A dermatoscopic image of a skin lesion.
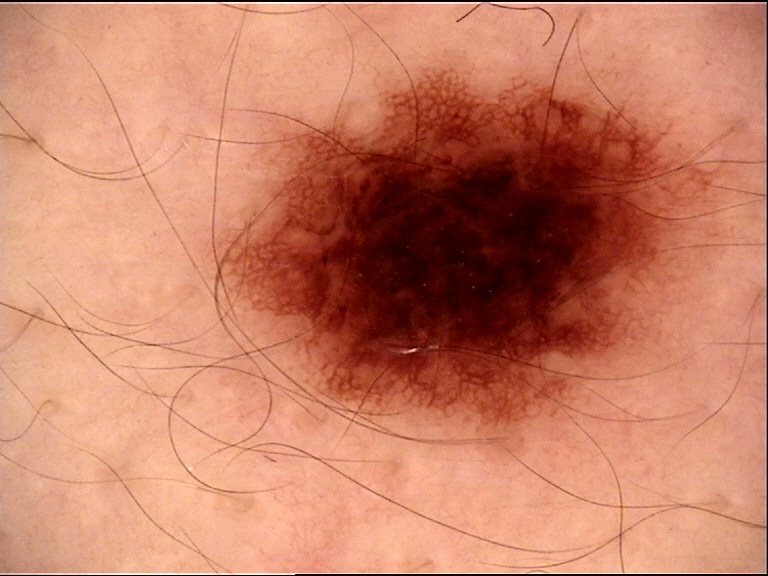The diagnostic label was a dysplastic compound nevus.